A dermoscopy image of a single skin lesion.
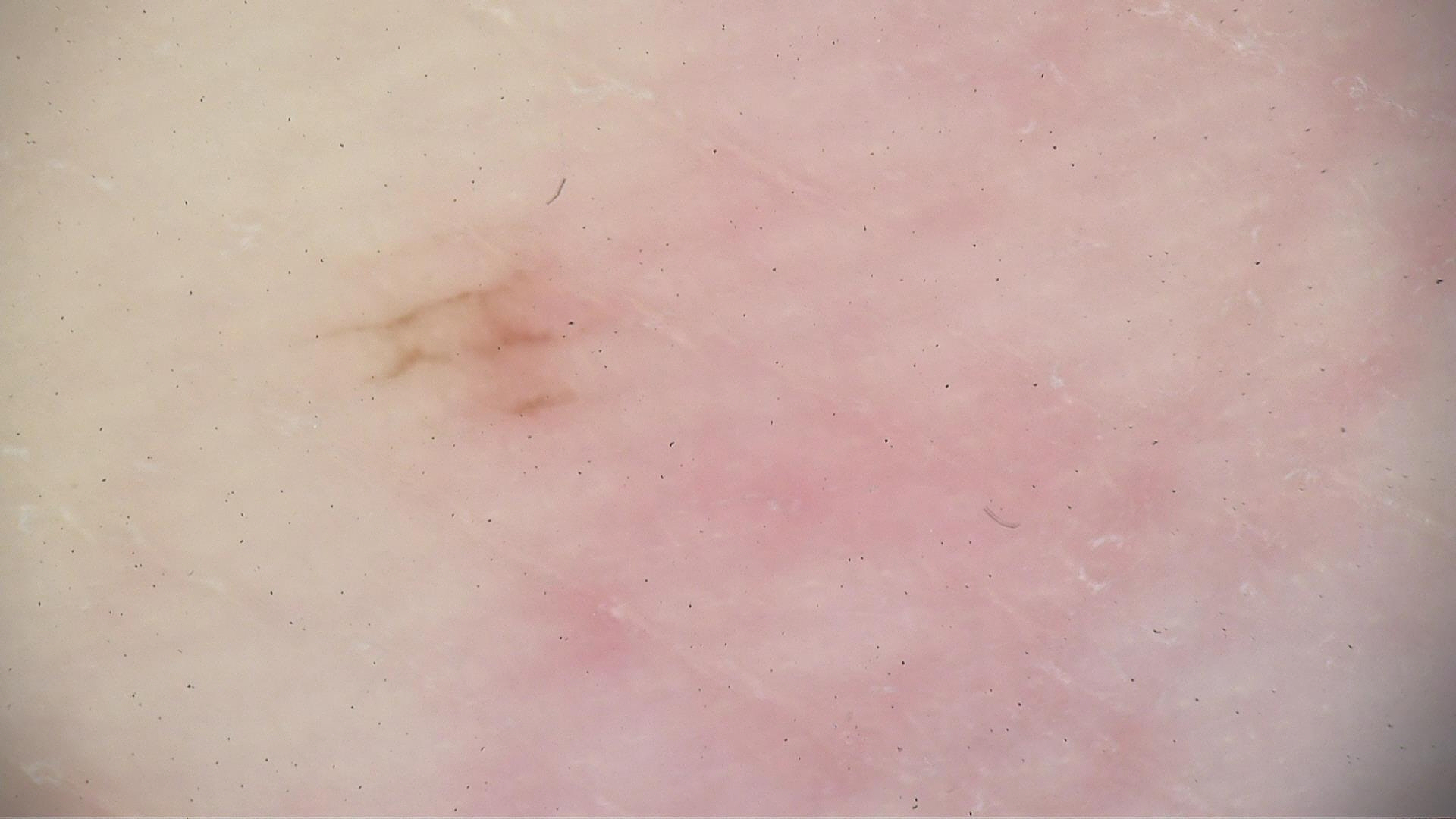Impression: The diagnosis was an acral dysplastic junctional nevus.